The photograph was taken at an angle:
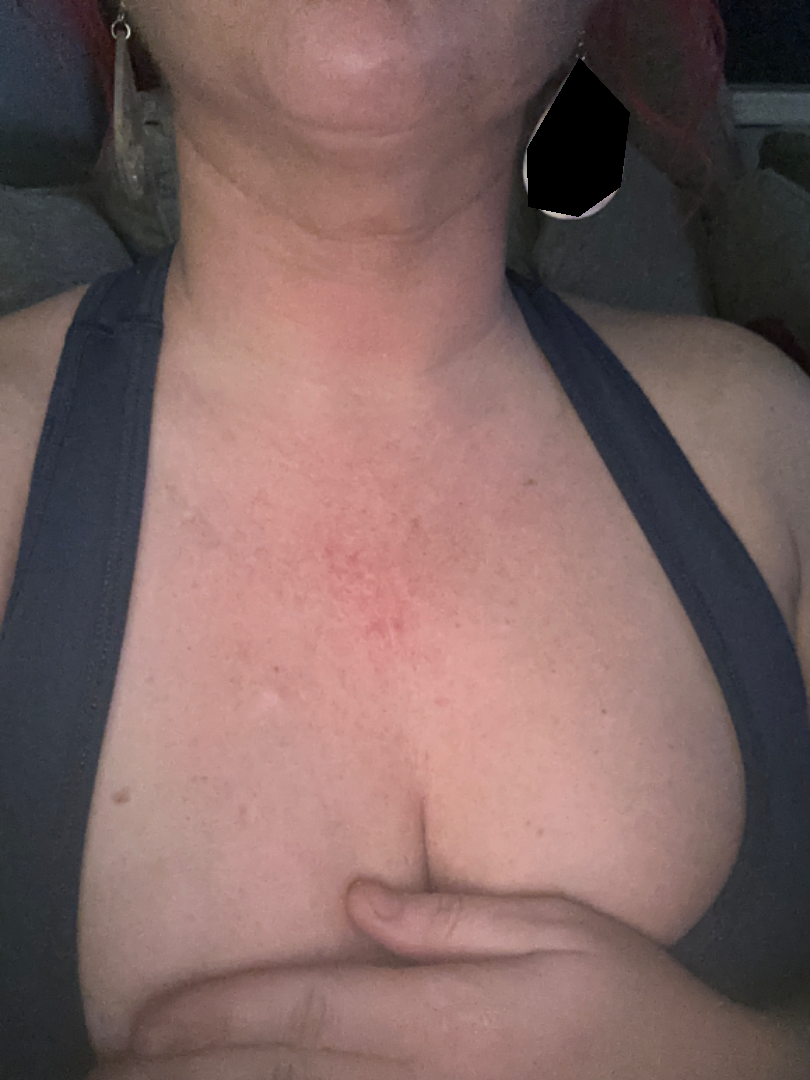Notes:
– assessment — unable to determine